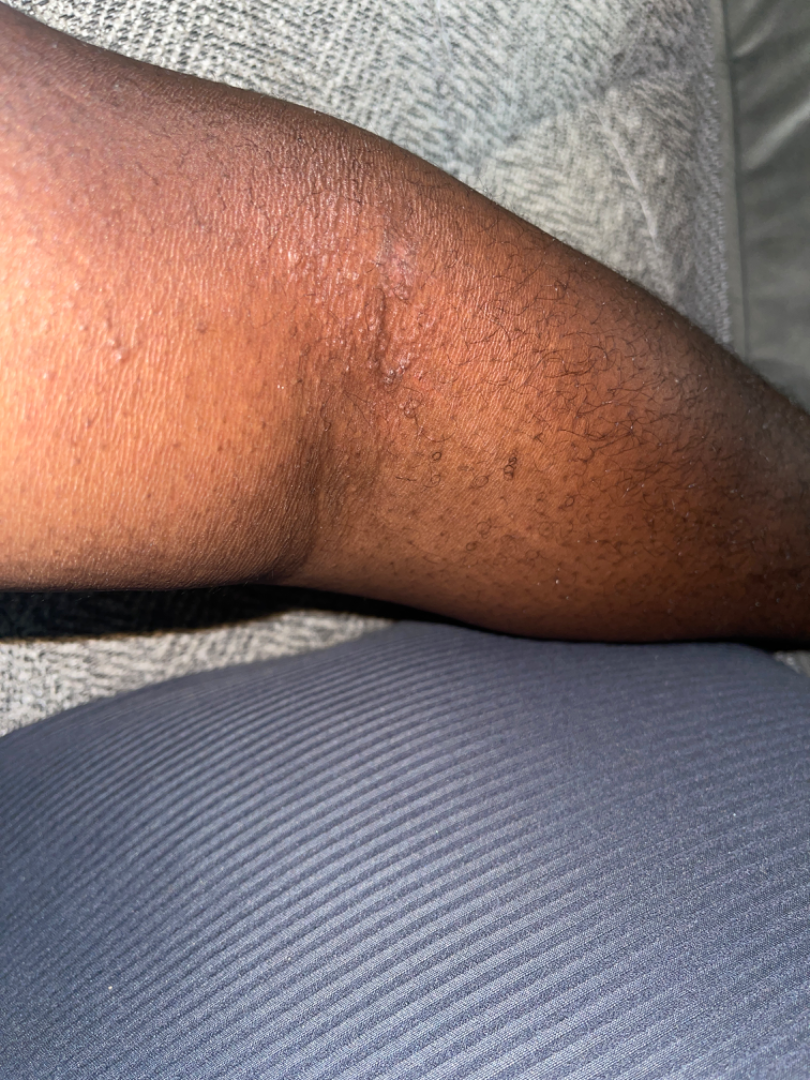assessment = in keeping with Eczema